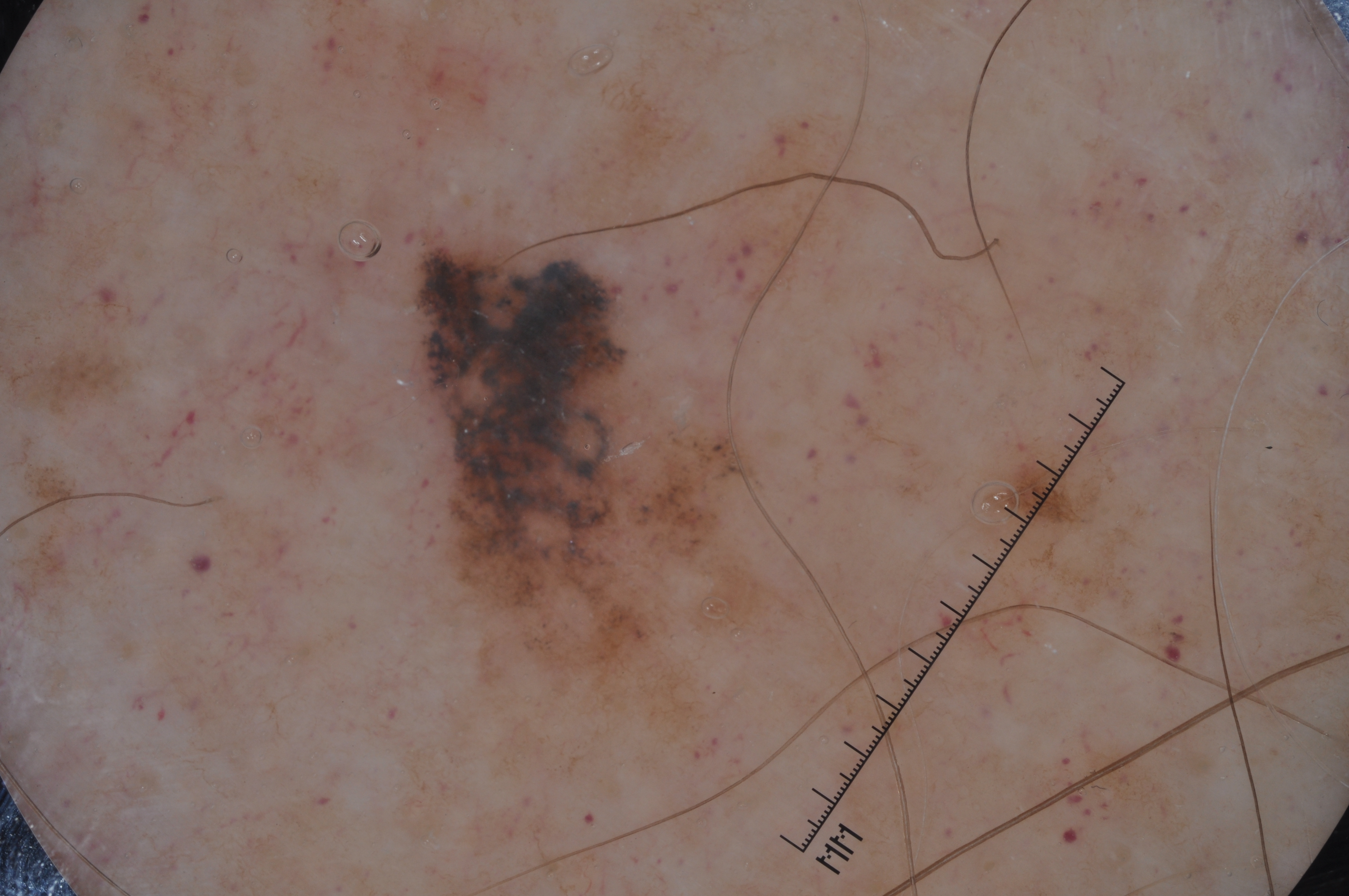patient:
  sex: male
  age_approx: 75
image:
  modality: dermoscopy
lesion_extent:
  approx_field_fraction_pct: 10
dermoscopic_features:
  present: []
  absent:
    - pigment network
    - streaks
    - milia-like cysts
    - negative network
lesion_location:
  bbox_xyxy:
    - 411
    - 239
    - 795
    - 737
diagnosis:
  name: melanoma
  malignancy: malignant
  lineage: melanocytic
  provenance: histopathology